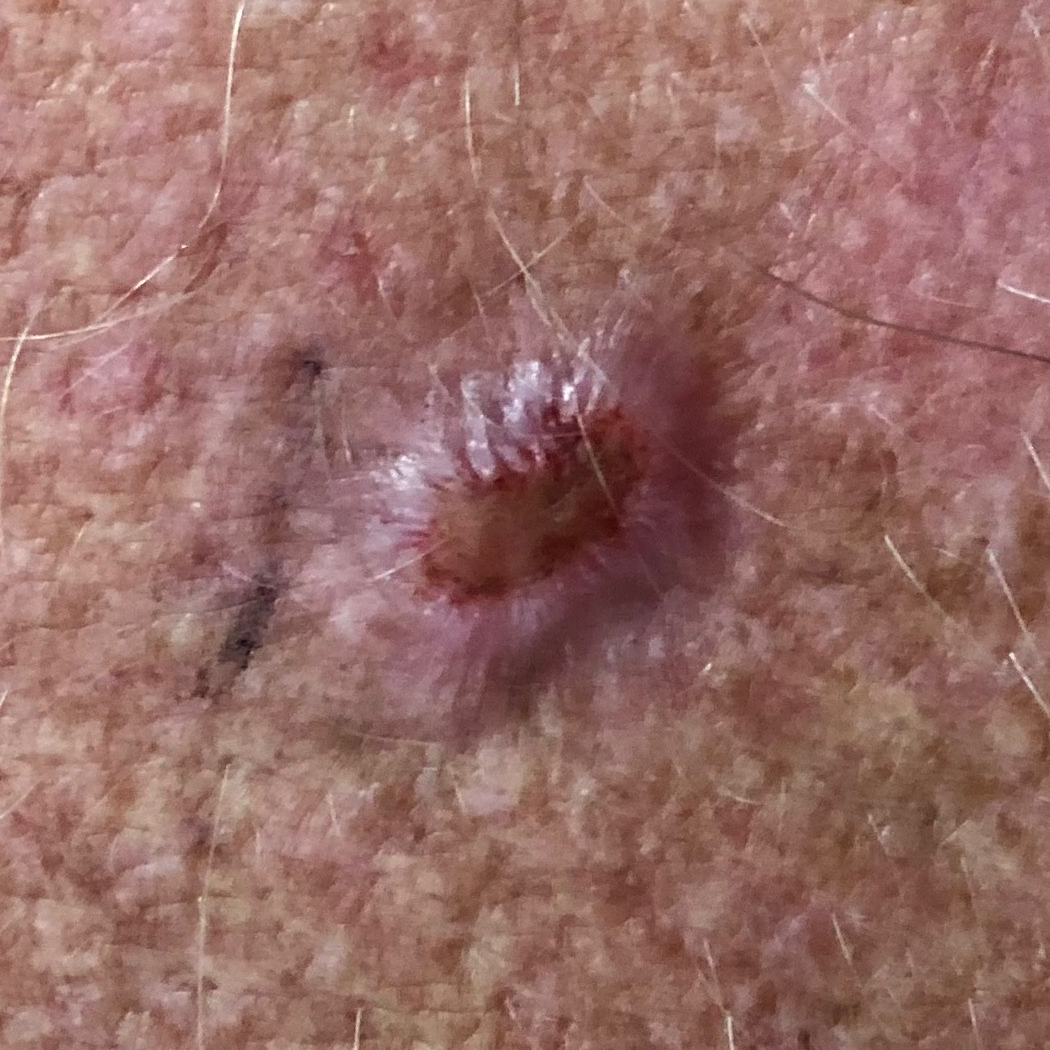The lesion is on the chest. The patient describes that the lesion itches, hurts, is elevated, and has bled. Histopathologically confirmed as a basal cell carcinoma.